A clinical close-up of a skin lesion; the patient reports a personal history of cancer, a personal history of skin cancer, a family history of skin cancer, and no prior organ transplant; a female patient 54 years of age; the patient says their skin reddens with sun exposure; the patient describes having numerous moles; collected as part of a research study, without a referral diagnosis — 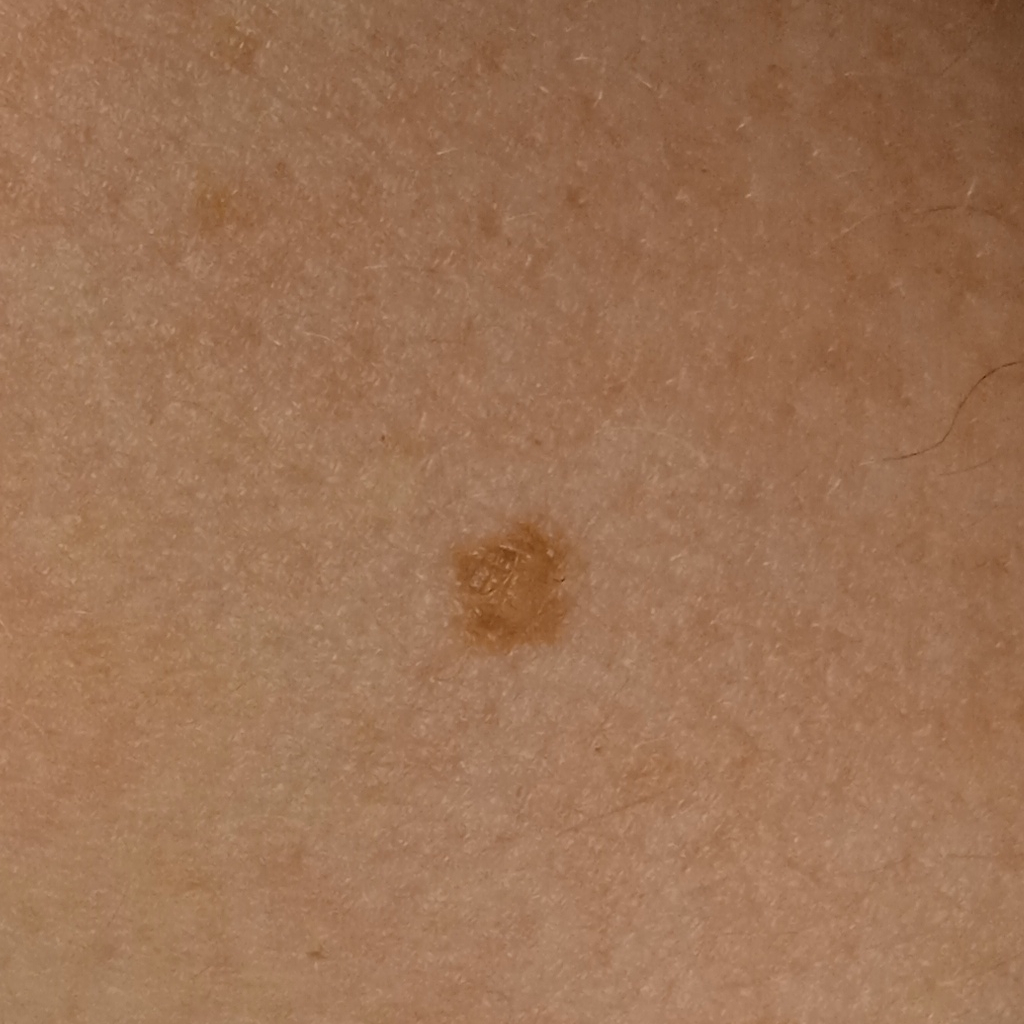Case summary:
The lesion involves an arm. The lesion is about 4.7 mm across.
Conclusion:
The diagnostic impression was an atypical (dysplastic) nevus.